A dermoscopic close-up of a skin lesion.
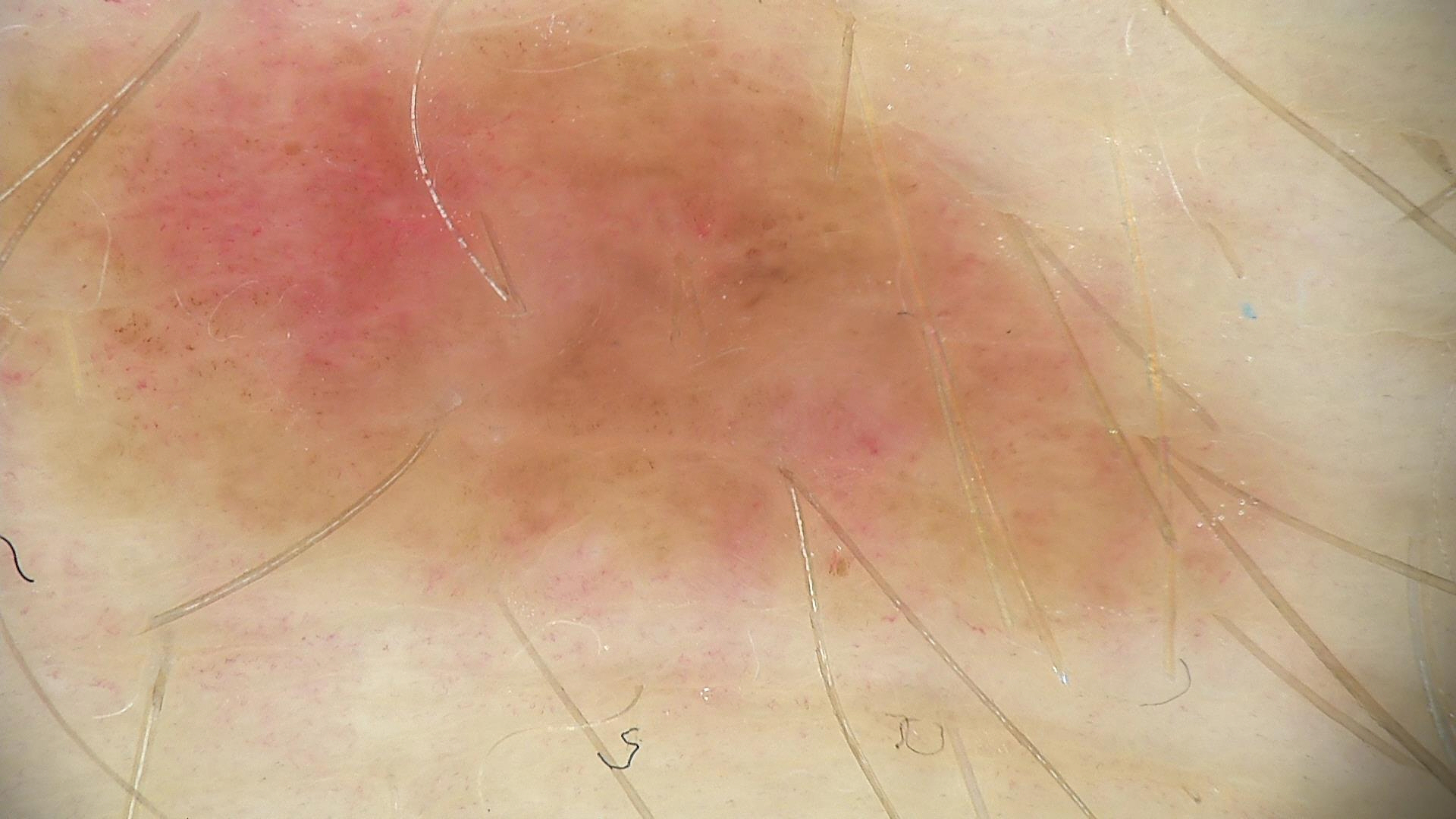Classified as a dysplastic junctional nevus.